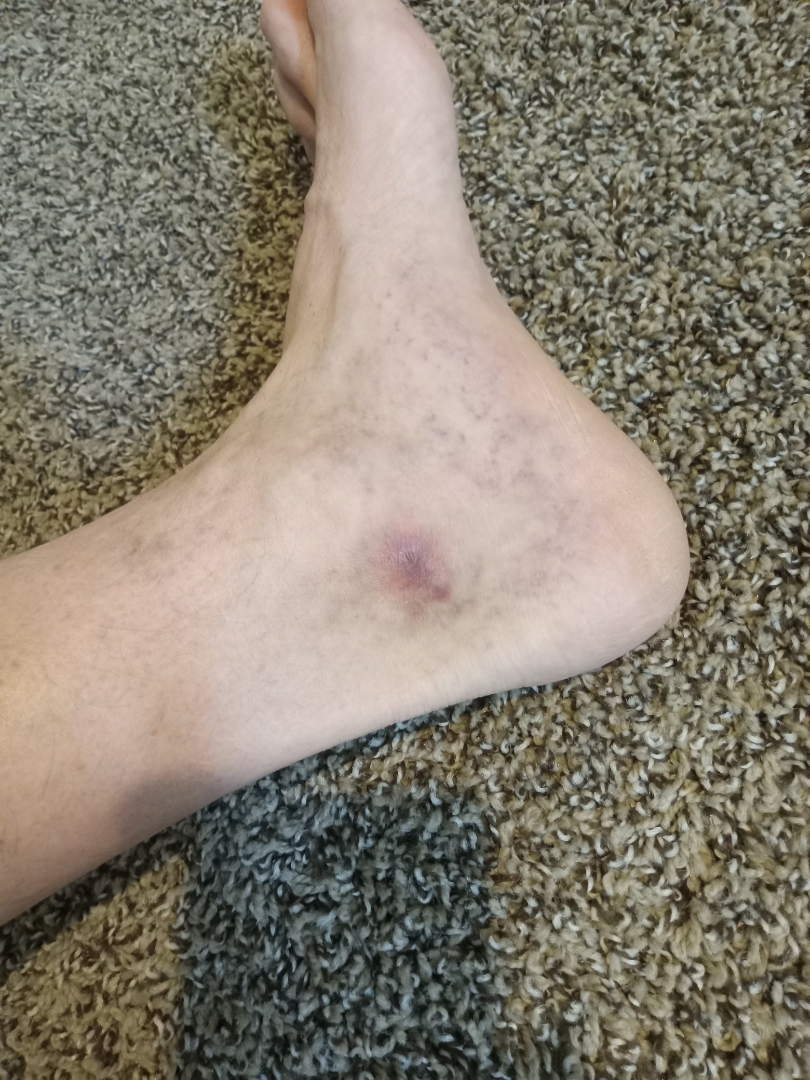Q: Reported symptoms?
A: bothersome appearance
Q: Duration?
A: less than one week
Q: How does the lesion feel?
A: flat and fluid-filled
Q: Where on the body?
A: top or side of the foot
Q: What is the framing?
A: at a distance
Q: Fitzpatrick or Monk tone?
A: Fitzpatrick III; lay graders estimated Monk Skin Tone 1 or 3 (two reviewer pools disagreed)
Q: What is the differential diagnosis?
A: in keeping with Venous Stasis Ulcer